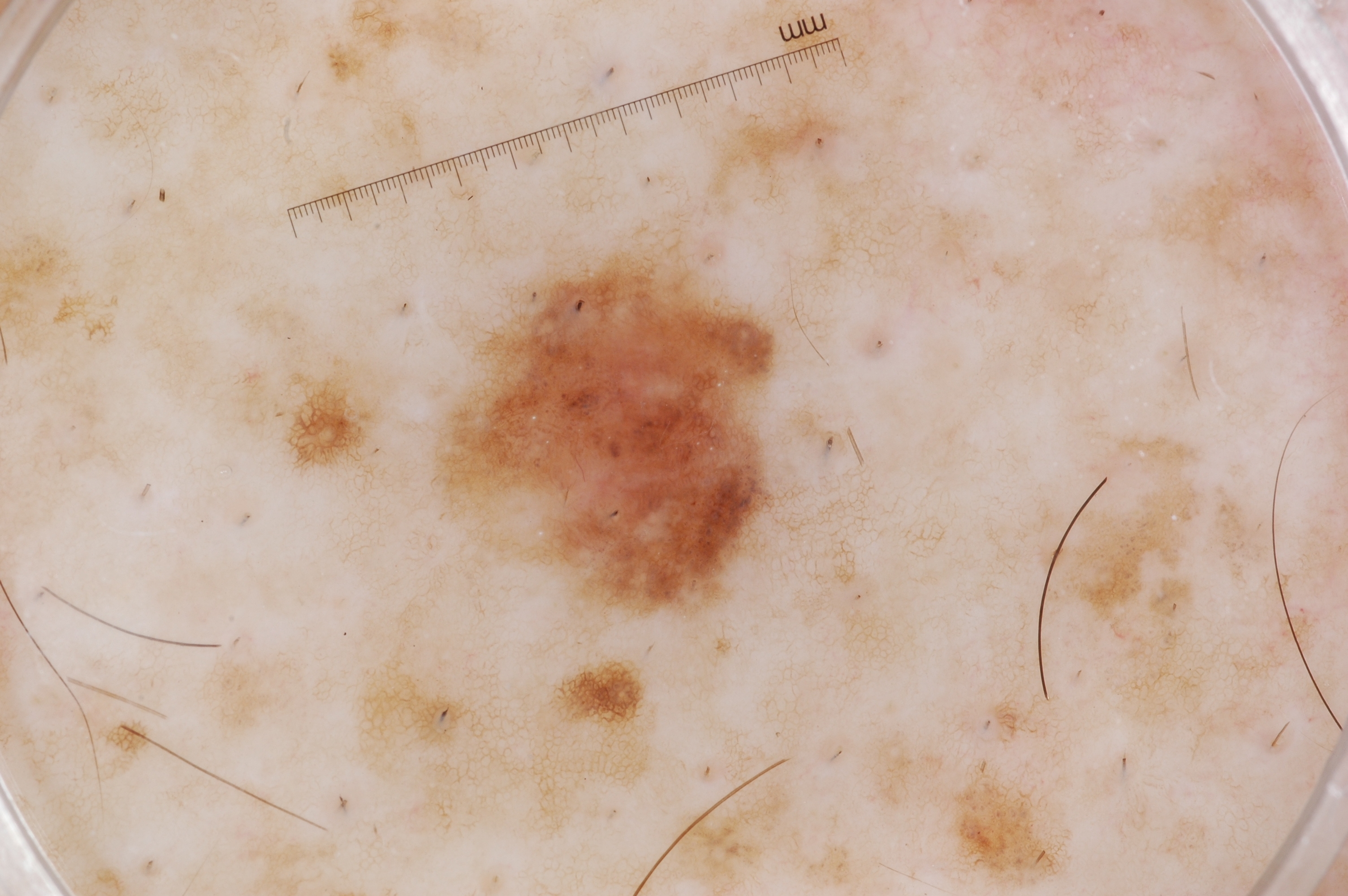Findings:
A male subject, in their mid-50s. A dermatoscopic image of a skin lesion. A small lesion within a wider field of skin. Dermoscopic assessment notes pigment network and milia-like cysts. The lesion spans box(453, 252, 779, 609).
Assessment:
Diagnosed as a melanocytic nevus, a benign skin lesion.